A dermoscopic view of a skin lesion · a male patient aged around 70: 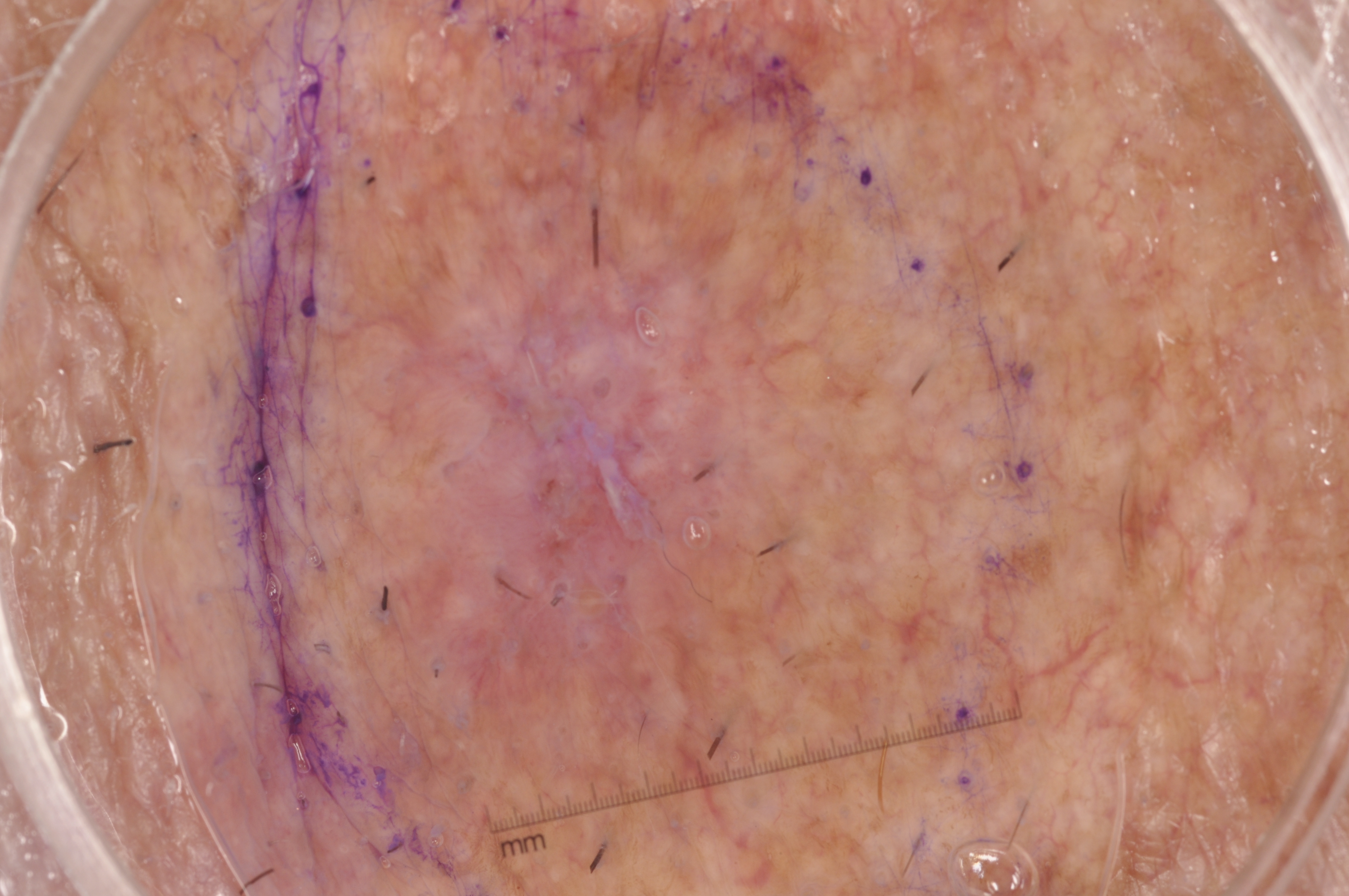Summary:
Dermoscopic examination shows no pigment network, streaks, negative network, or milia-like cysts. With coordinates (x1, y1, x2, y2), the lesion occupies the region [307,9,964,882]. The lesion takes up about 37% of the image.
Conclusion:
Expert review diagnosed this as a seborrheic keratosis, a non-melanocytic (keratinocytic) lesion.